This is a close-up image.
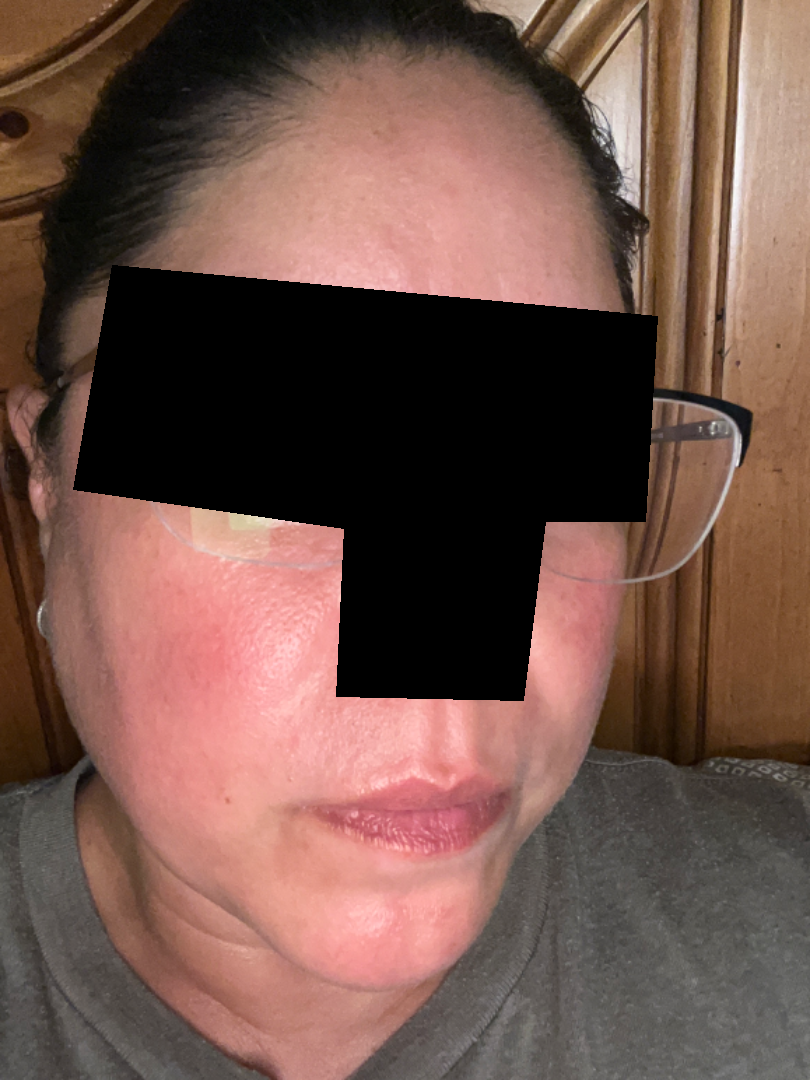Q: Reported symptoms?
A: bothersome appearance
Q: What is the lesion texture?
A: flat
Q: Duration?
A: less than one week
Q: How does the patient describe it?
A: skin that appeared healthy to them
Q: What conditions are considered?
A: Rosacea (0.41); Flushing (0.41); Cutaneous lupus (0.18)